By history, tobacco use and prior malignancy (patient or family); skin type II; a clinical photograph showing a skin lesion; a female patient age 66 — 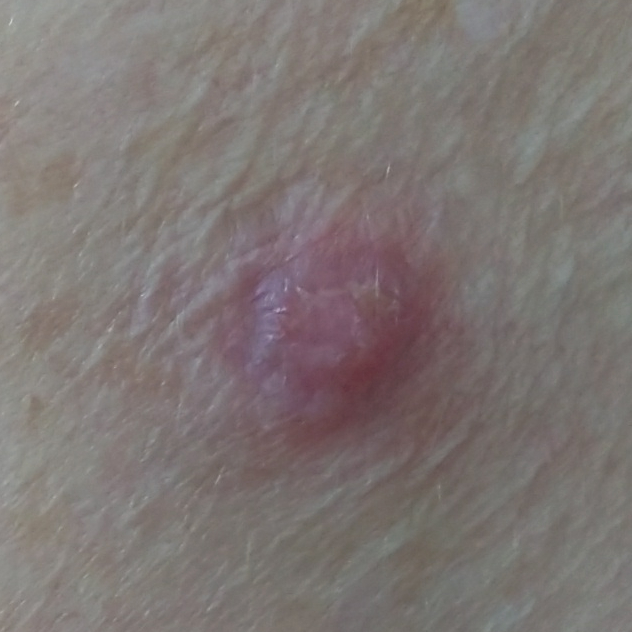Q: What is the anatomic site?
A: a forearm
Q: Any reported symptoms?
A: elevation, itching
Q: What did the workup show?
A: basal cell carcinoma (biopsy-proven)